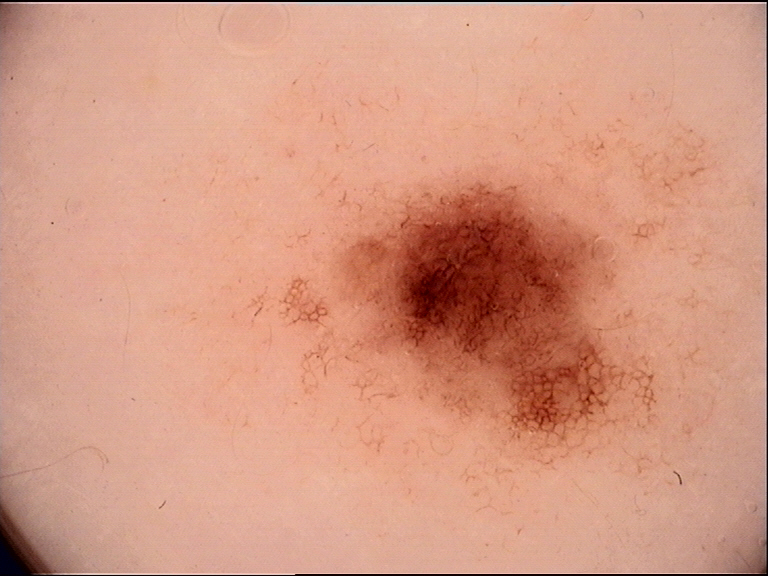Case:
• image — dermoscopy
• label — dysplastic junctional nevus (expert consensus)